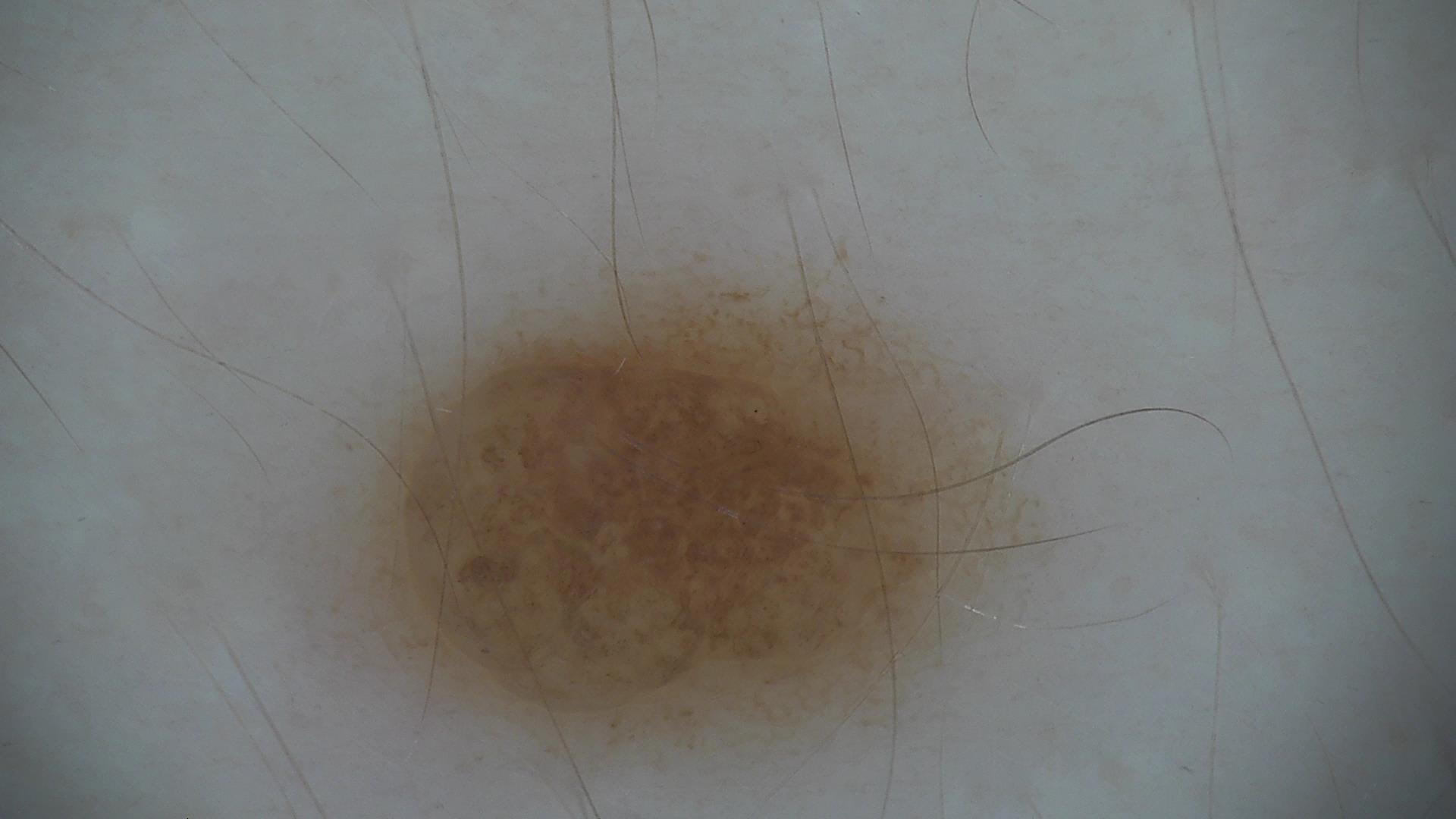Impression: Labeled as a compound nevus.